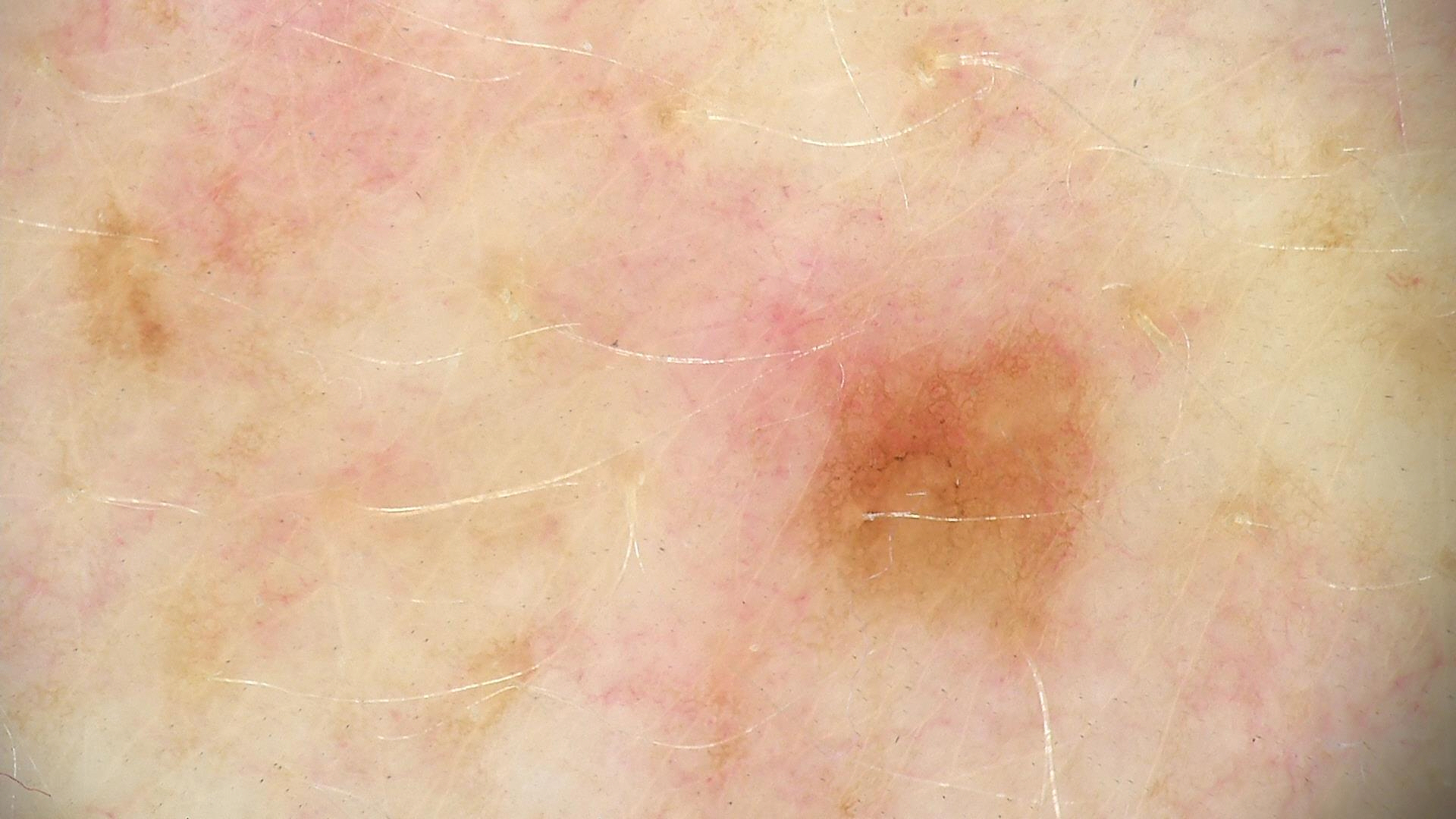modality = dermoscopy | diagnostic label = dysplastic junctional nevus (expert consensus).